The lesion involves the arm · a close-up photograph · the contributor is 60–69, female.
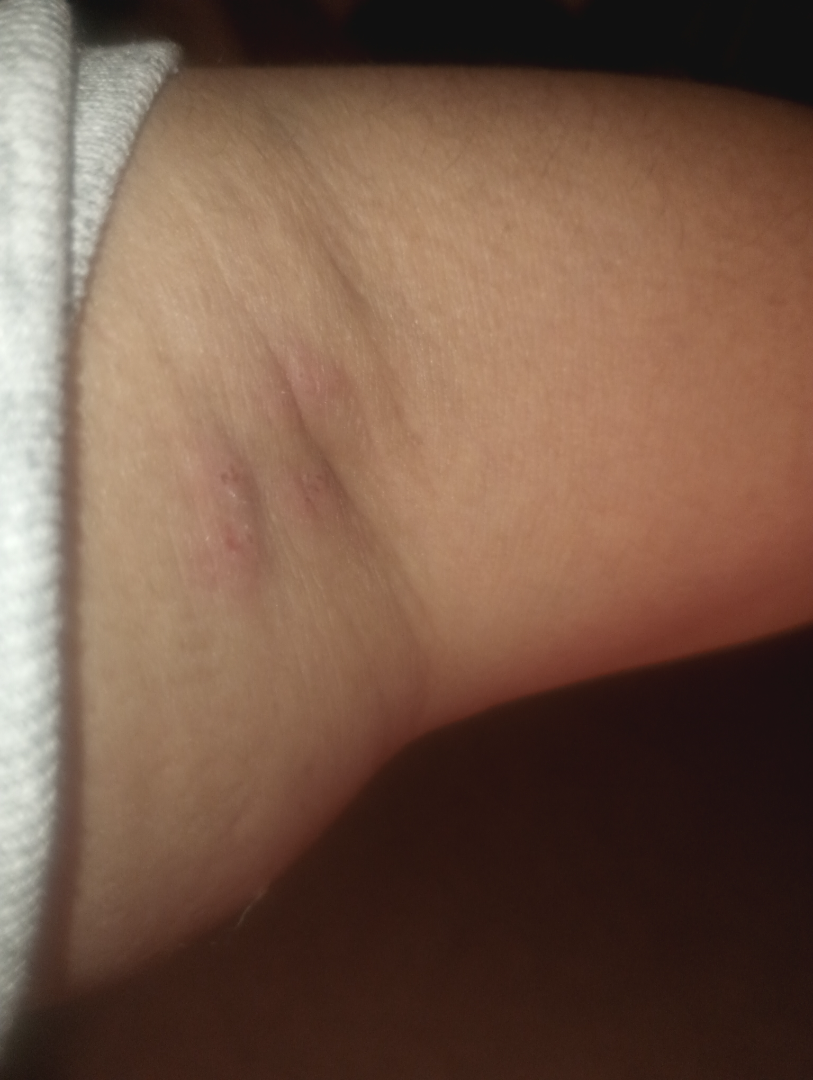History: No constitutional symptoms were reported. Texture is reported as raised or bumpy. Self-categorized by the patient as a rash. Impression: On dermatologist assessment of the image: Abscess and Hidradenitis were each considered, in no particular order.